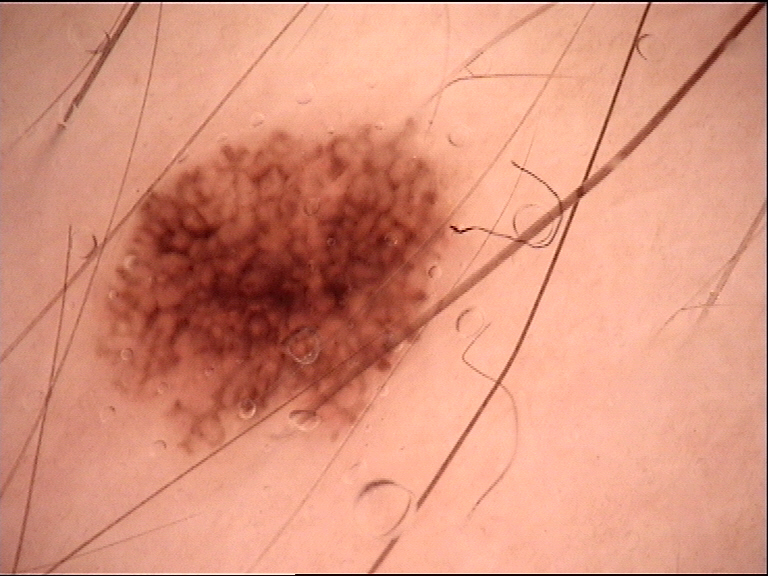A dermatoscopic image of a skin lesion. Diagnosed as a benign lesion — a dysplastic junctional nevus.